A dermatoscopic image of a skin lesion.
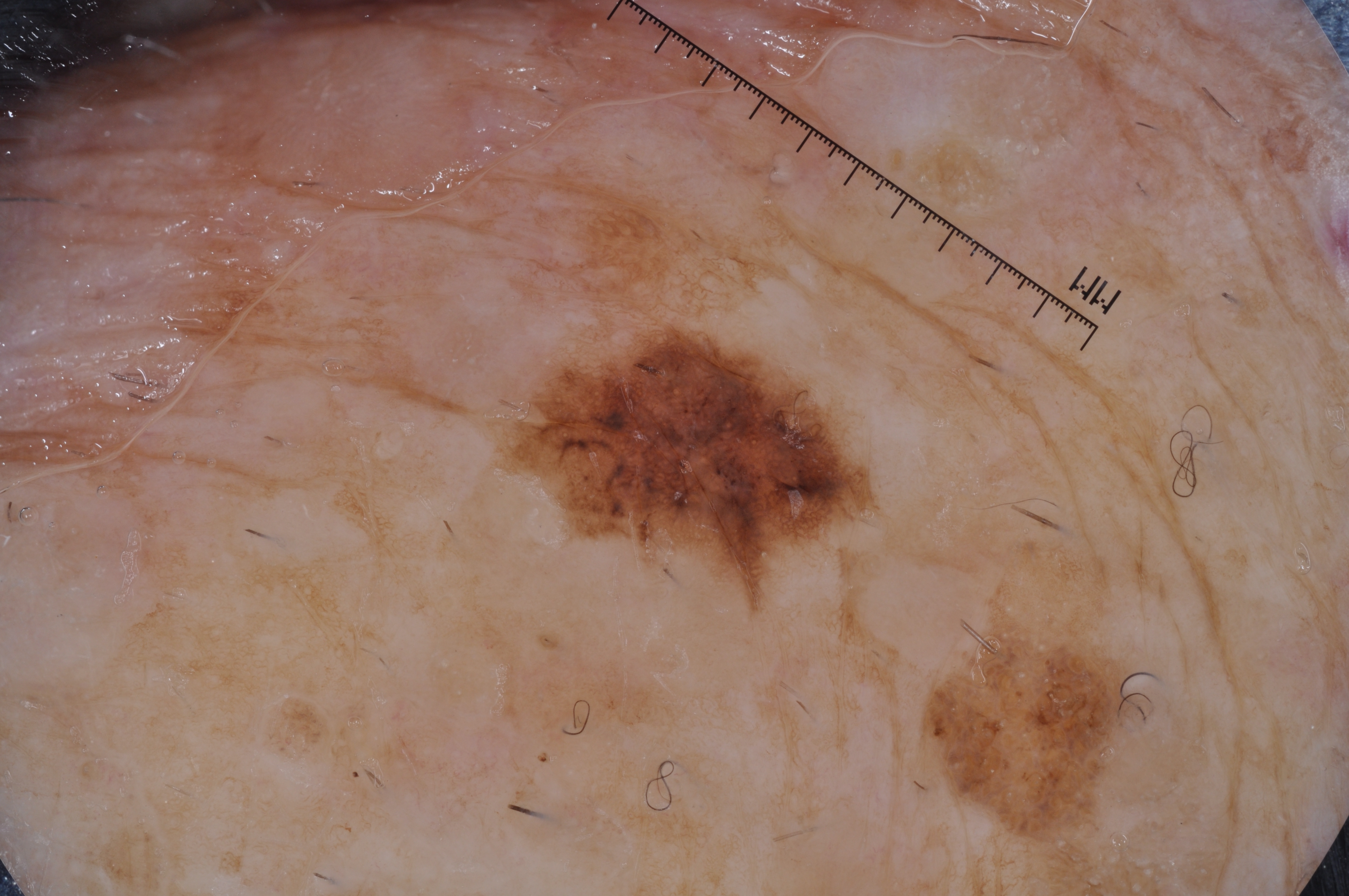lesion_location:
  bbox_xyxy:
    - 473
    - 314
    - 890
    - 615
dermoscopic_features:
  present:
    - pigment network
  absent:
    - streaks
    - negative network
    - milia-like cysts
diagnosis:
  name: melanoma
  malignancy: malignant
  lineage: melanocytic
  provenance: histopathology